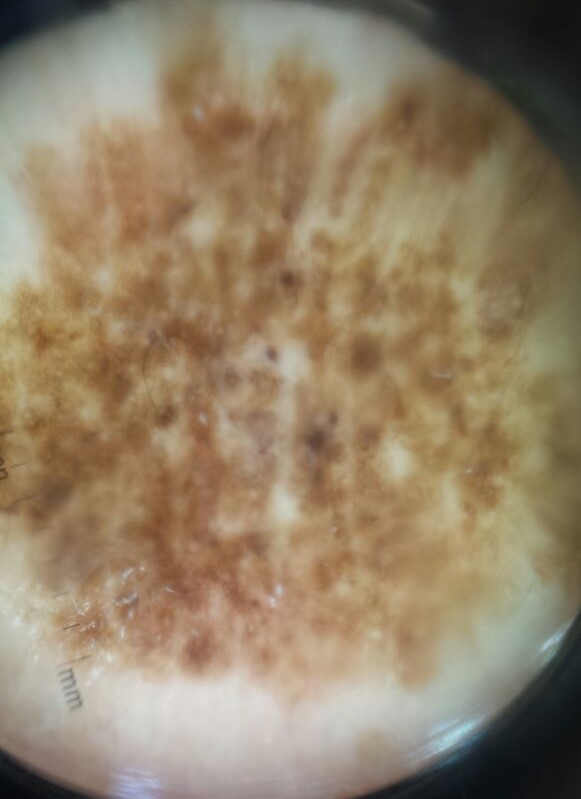A dermoscopic image of a skin lesion.
The diagnostic label was a benign lesion — a congenital dysplastic compound nevus.